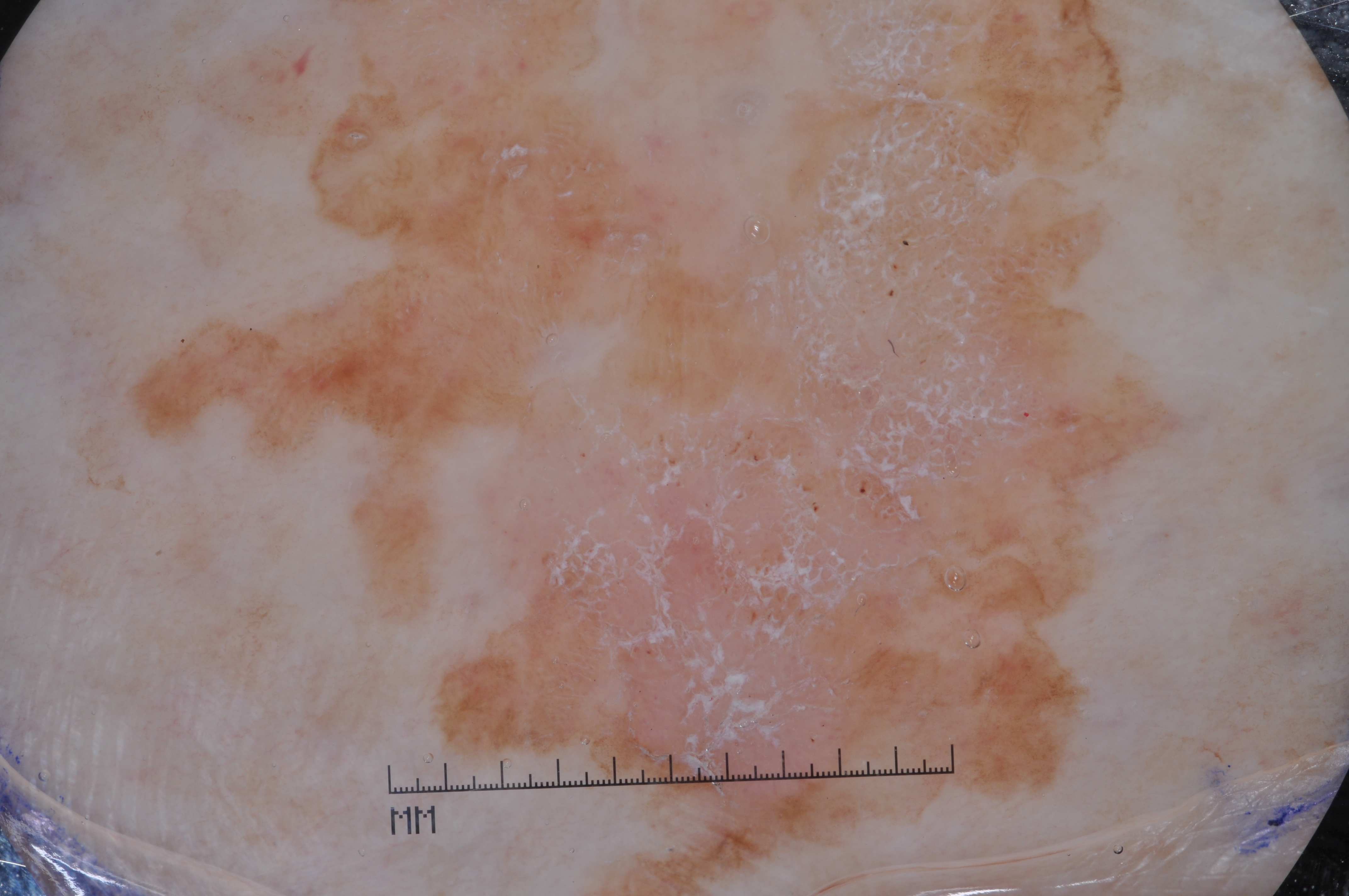A dermoscopy image of a single skin lesion. The patient is a female in their 70s. The lesion is bounded by x1=116, y1=0, x2=1180, y2=895. The lesion is clipped by the edge of the image. The lesion takes up a large portion of the image. Dermoscopically, the lesion shows no milia-like cysts, negative network, streaks, or pigment network. The clinical diagnosis was a seborrheic keratosis, a benign skin lesion.